A male patient aged 73-77: 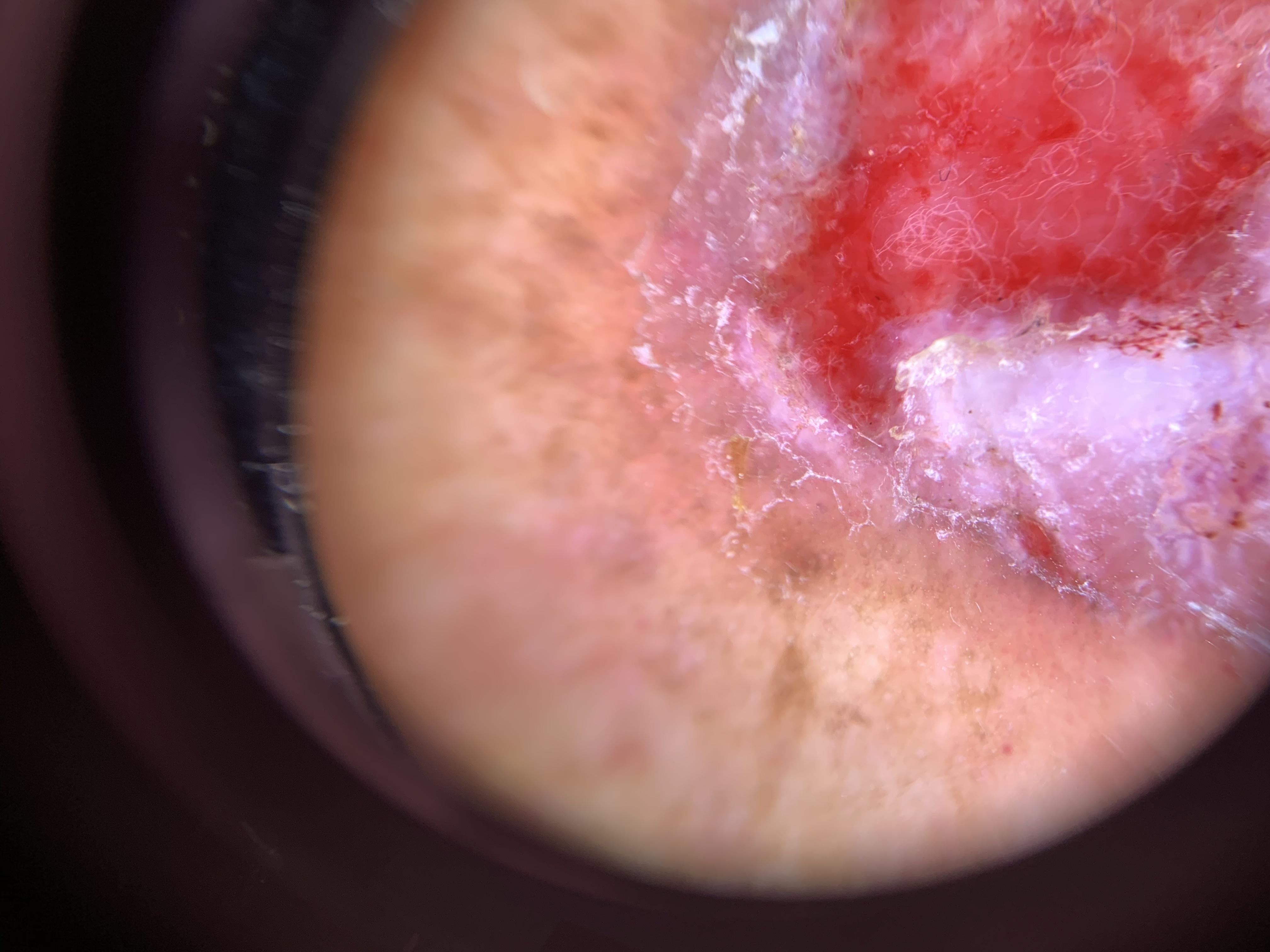Findings:
- pathology · Basal cell carcinoma (biopsy-proven)